The lesion involves the arm · female patient, age 50–59 · close-up view:
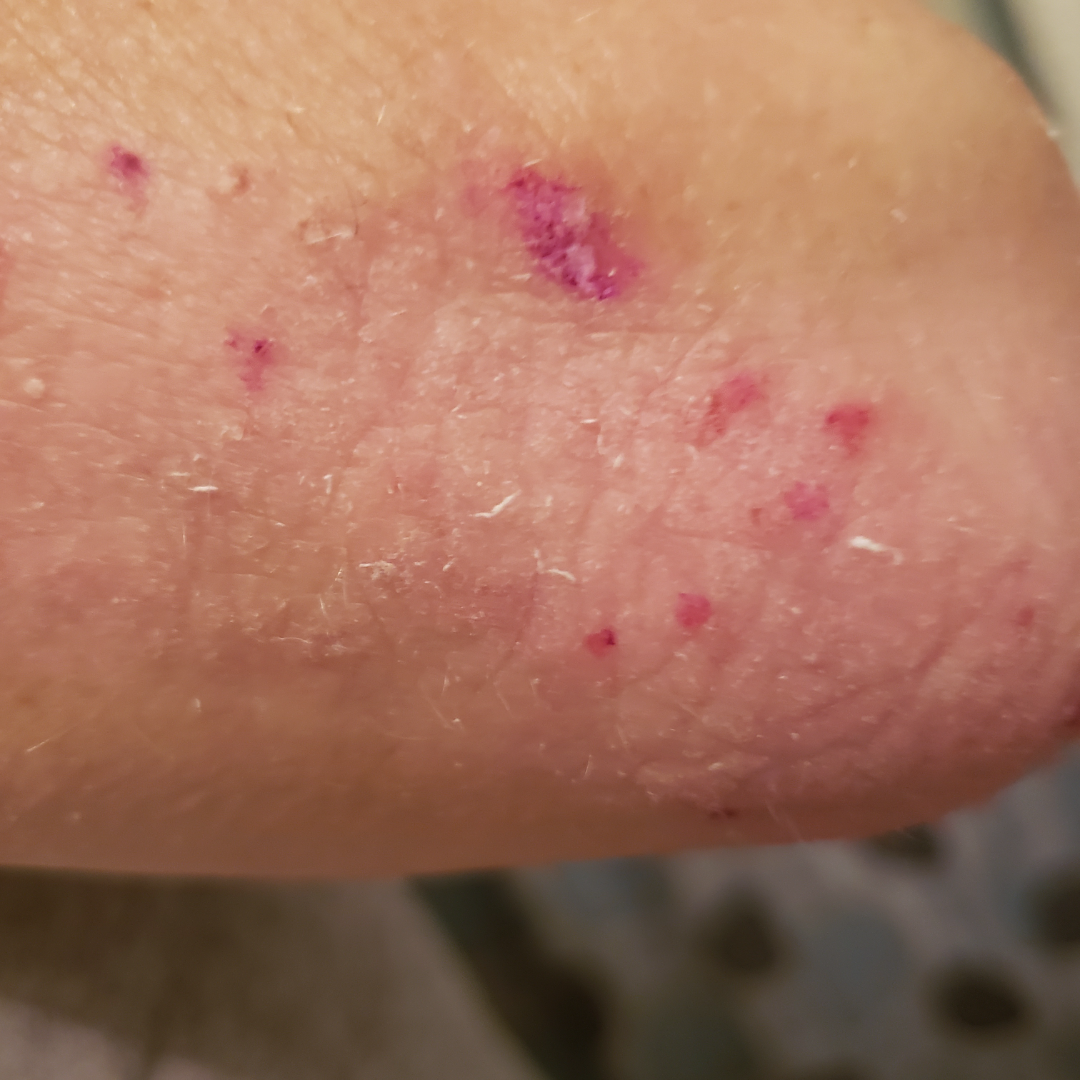Texture is reported as raised or bumpy and rough or flaky. In keeping with Psoriasis.